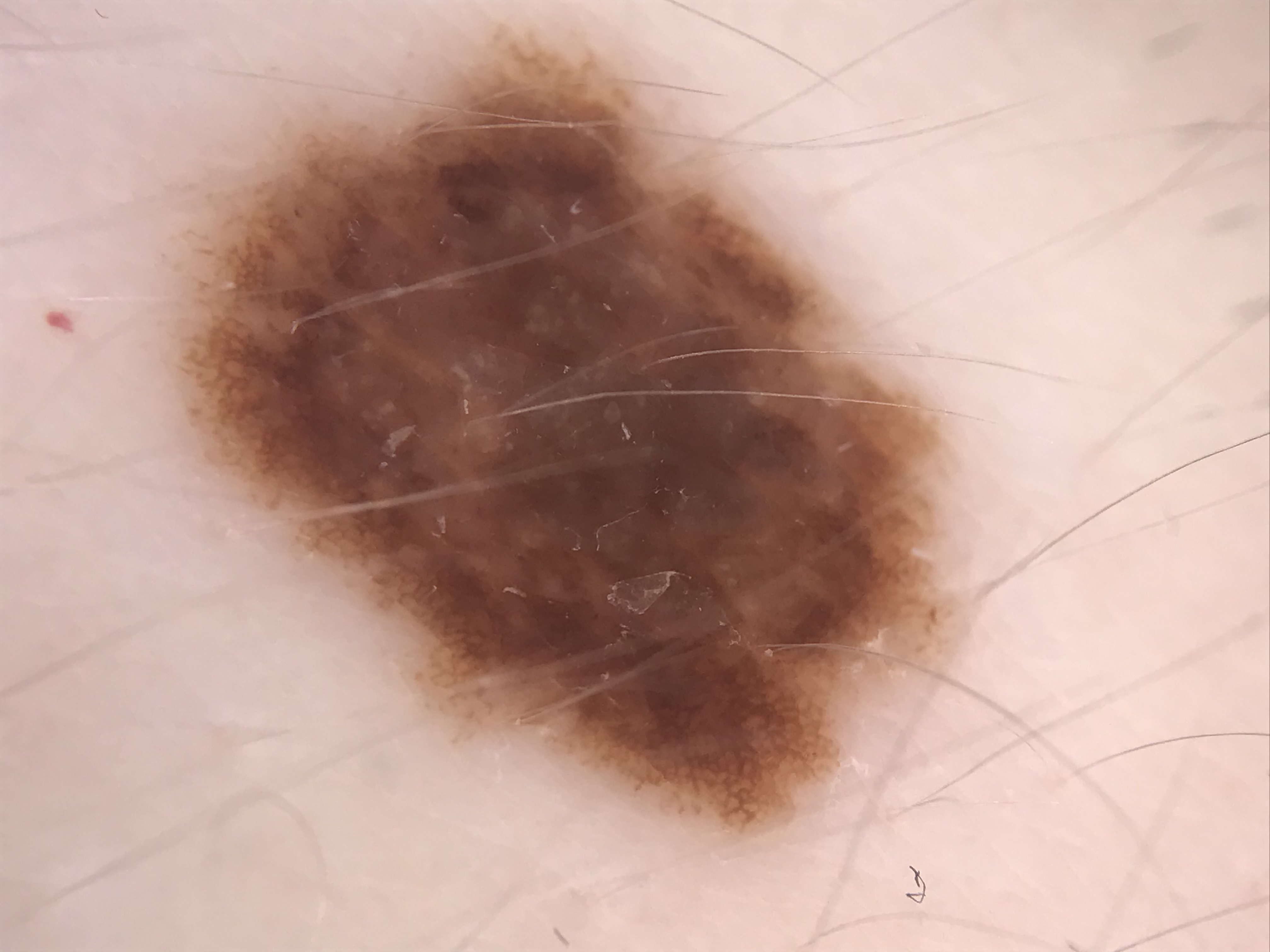Summary: A dermatoscopic image of a skin lesion. Conclusion: Classified as a benign lesion — a dysplastic compound nevus.